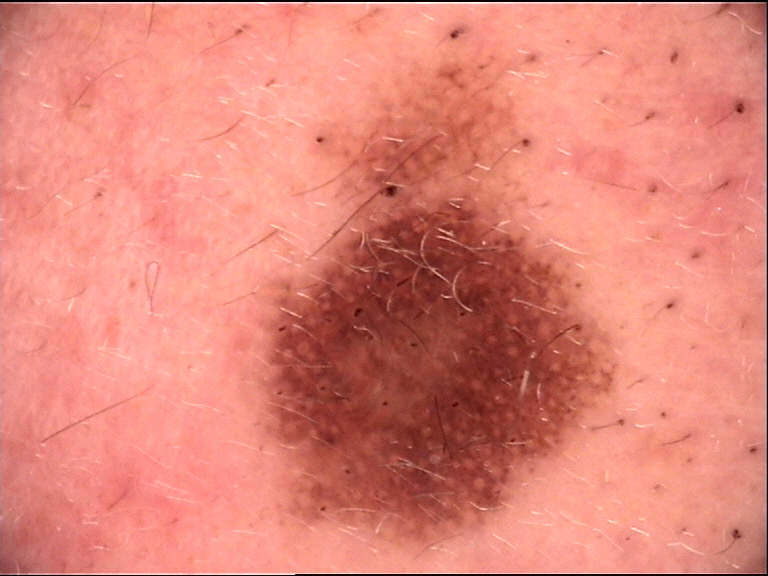label: Miescher nevus (expert consensus)